A dermoscopic view of a skin lesion. A female patient approximately 40 years of age.
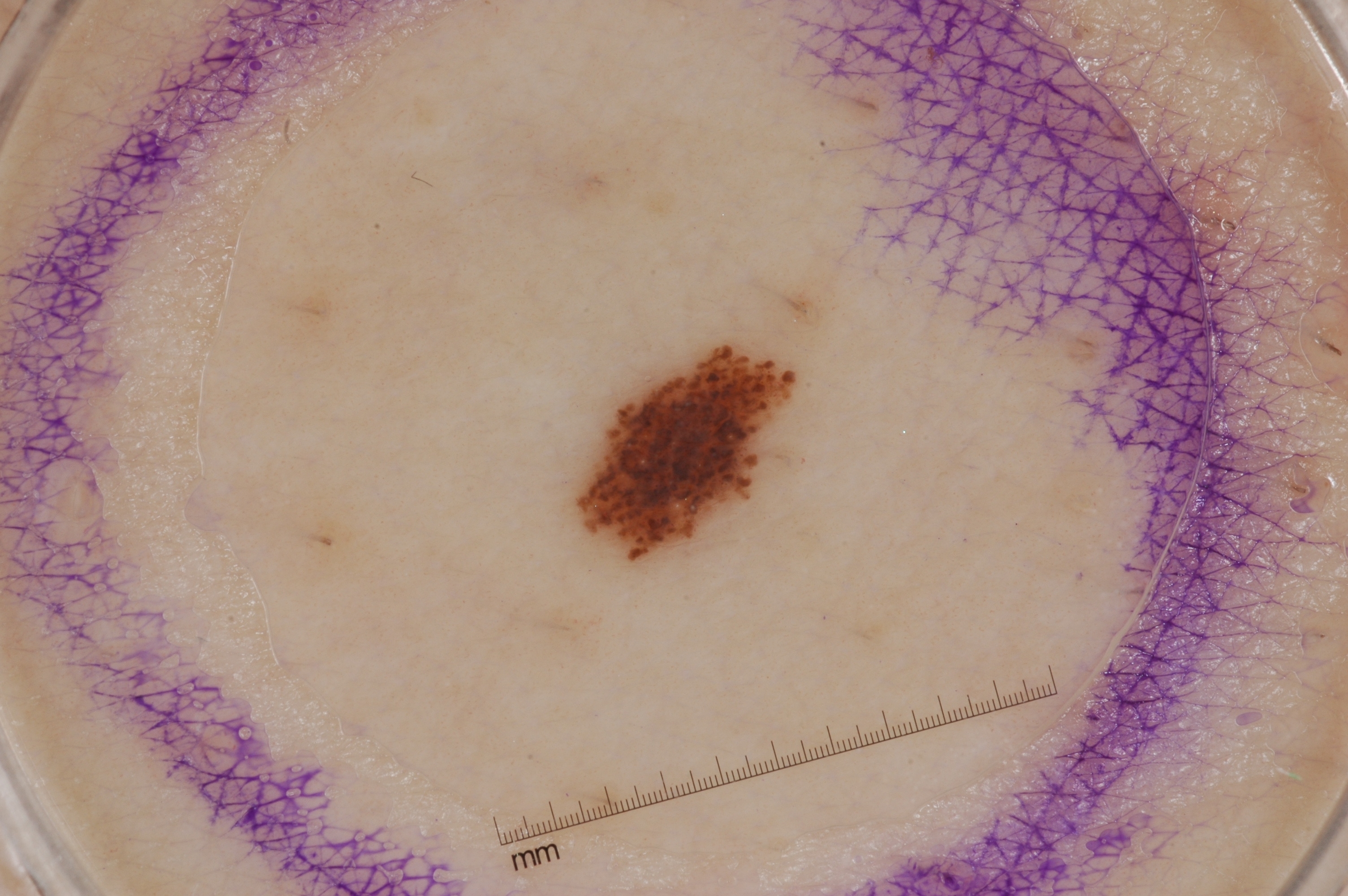Dermoscopically, the lesion shows streaks and milia-like cysts; no negative network or pigment network.
The lesion occupies the region x1=579 y1=350 x2=790 y2=560.
The diagnostic assessment was a melanocytic nevus, a benign lesion.